A dermoscopy image of a single skin lesion: 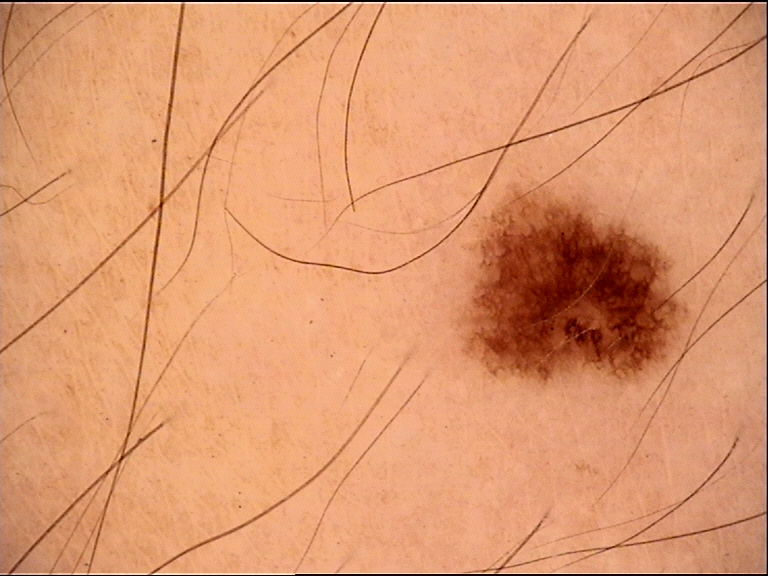Case: The architecture is that of a banal lesion. Conclusion: Diagnosed as a junctional nevus.